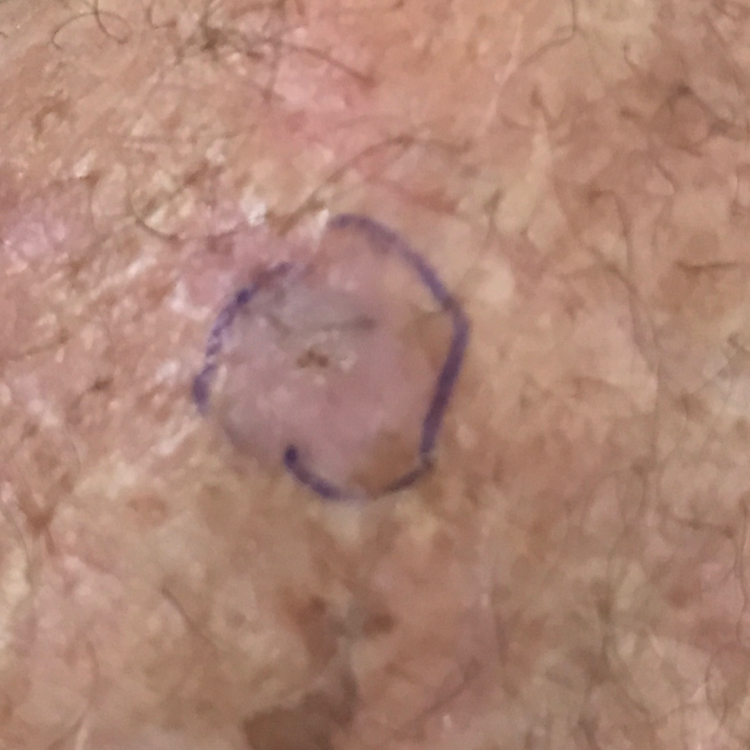The consensus clinical diagnosis was an actinic keratosis.